The subject is male. The leg is involved. Symptoms reported: itching. Fitzpatrick phototype V. The contributor notes the lesion is raised or bumpy. The condition has been present for one to four weeks. The photo was captured at an angle:
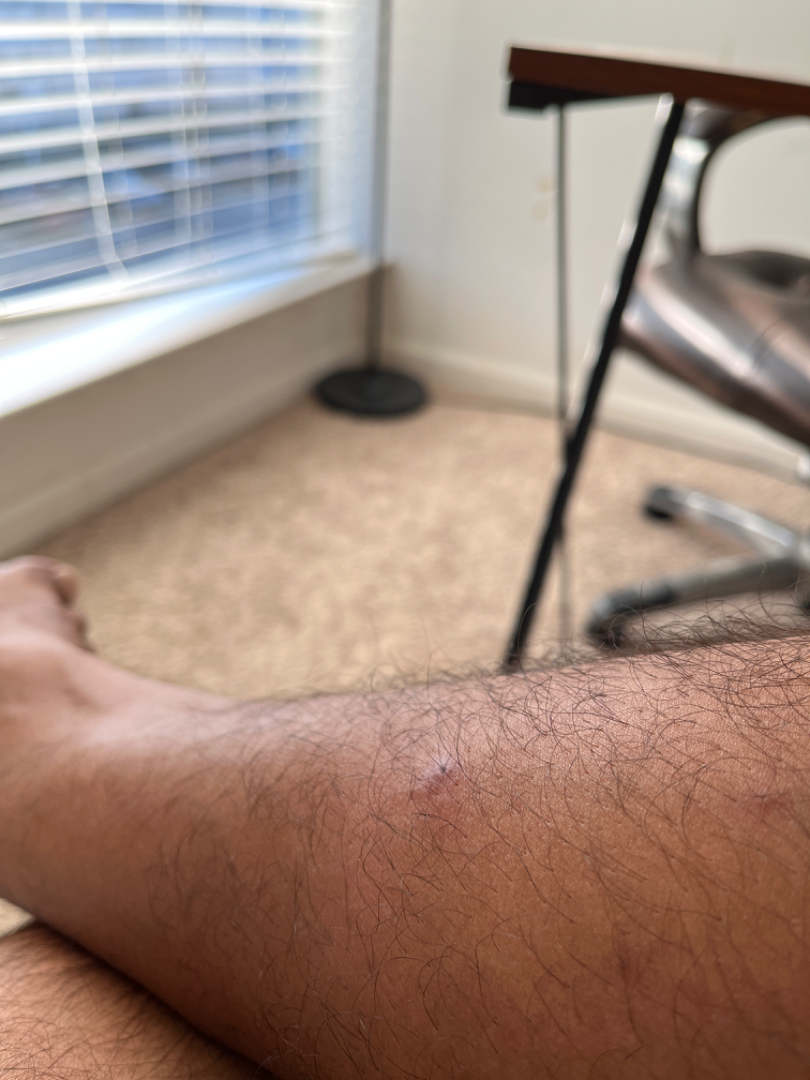Findings:
Reviewed remotely by one dermatologist: most consistent with Abscess.